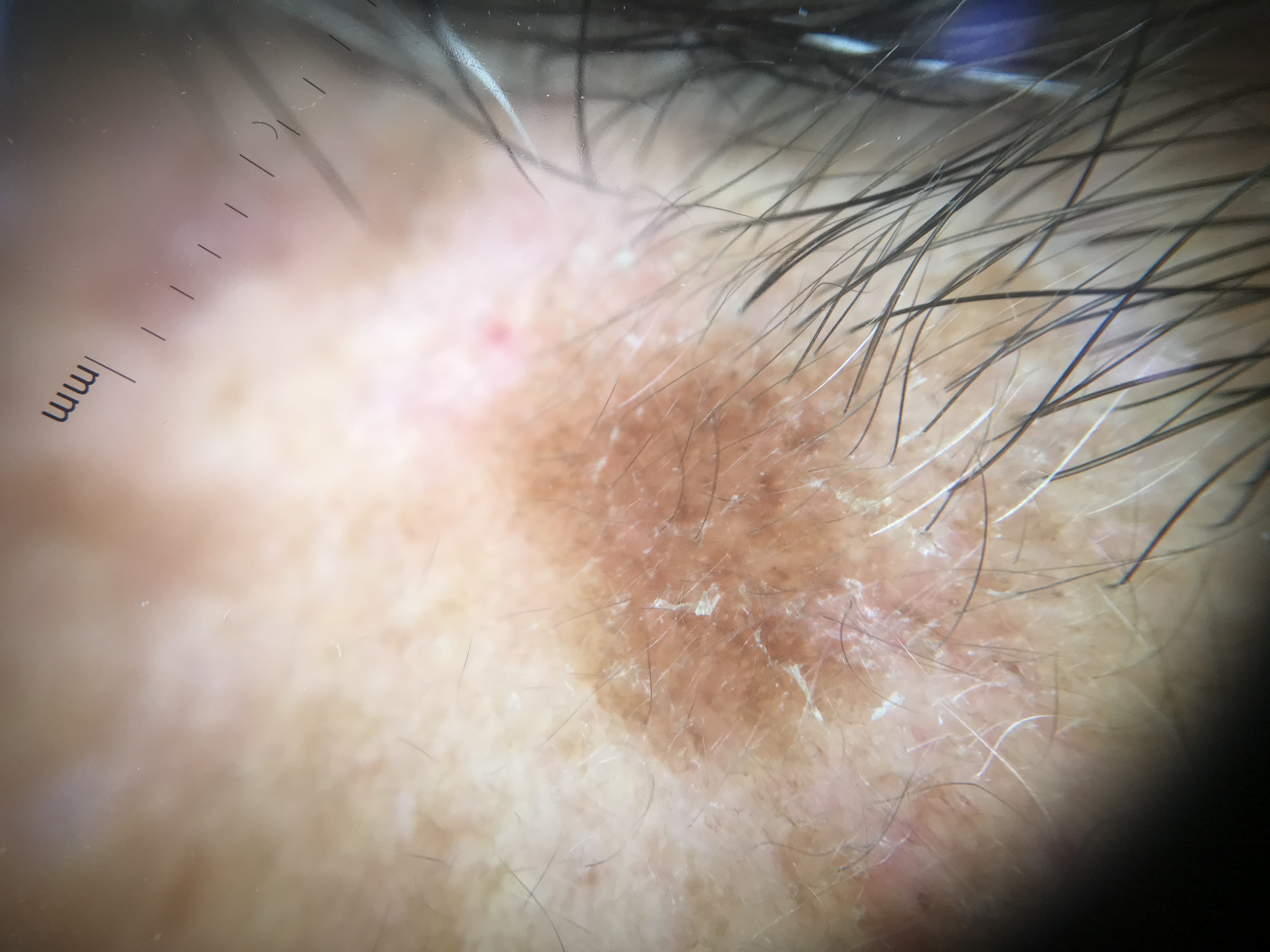Conclusion:
The diagnosis was a seborrheic keratosis.